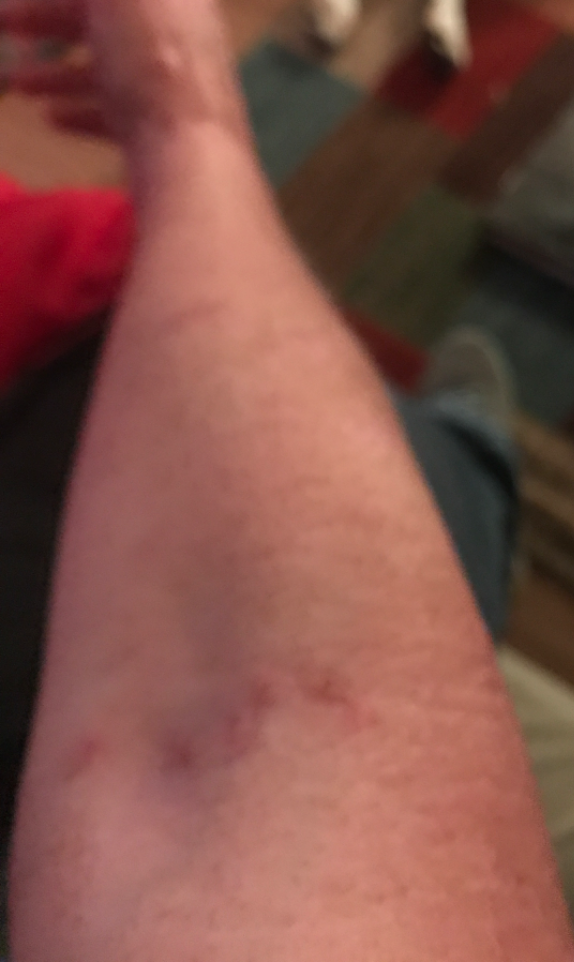reported symptoms — enlargement, bothersome appearance, burning, itching, pain and bleeding; skin tone — Fitzpatrick III; view — close-up; anatomic site — back of the torso, arm, back of the hand, front of the torso and head or neck; patient's own categorization — a rash; lesion texture — raised or bumpy; subject — female, age 50–59; history — one to four weeks; dermatologist impression — the differential, in no particular order, includes Folliculitis and Insect Bite.